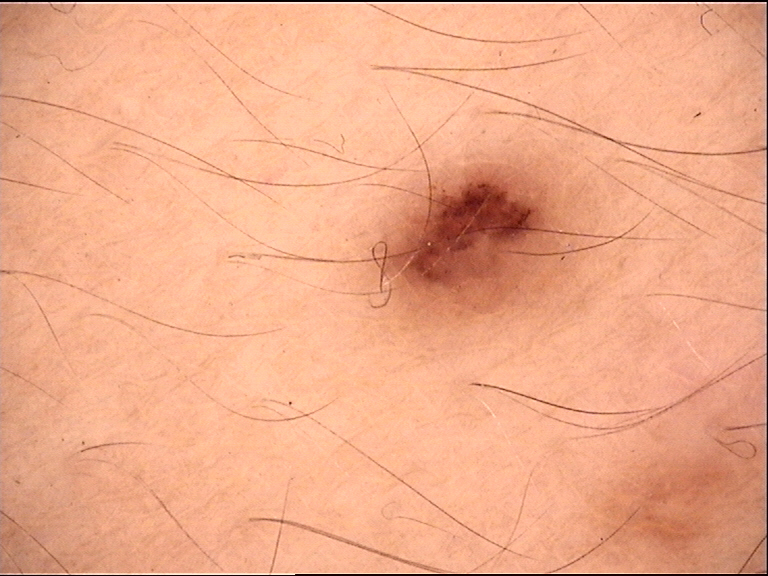- assessment — dysplastic junctional nevus (expert consensus)